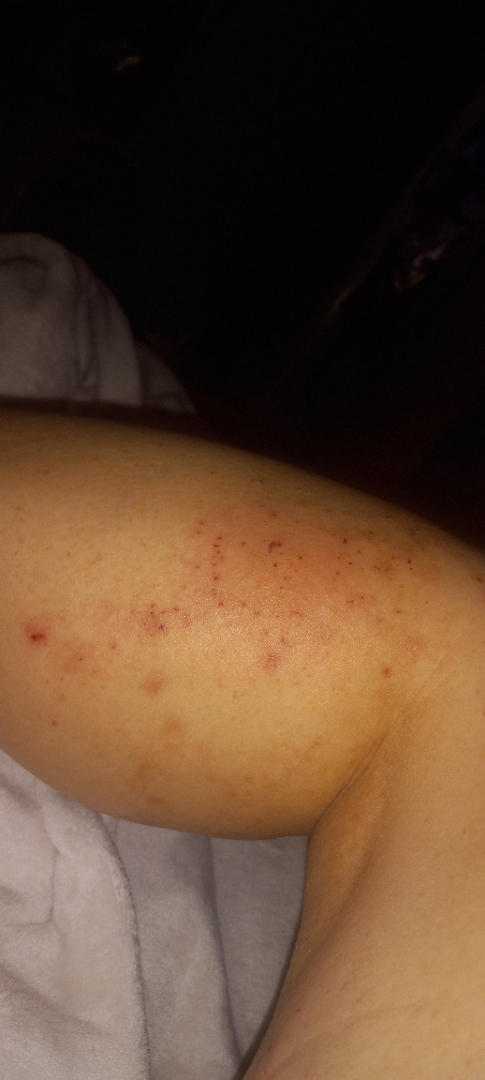assessment: unable to determine
described texture: rough or flaky
symptom duration: one to four weeks
affected area: arm, leg and top or side of the foot
self-categorized as: a rash
subject: female
reported symptoms: bleeding and itching
framing: at a distance